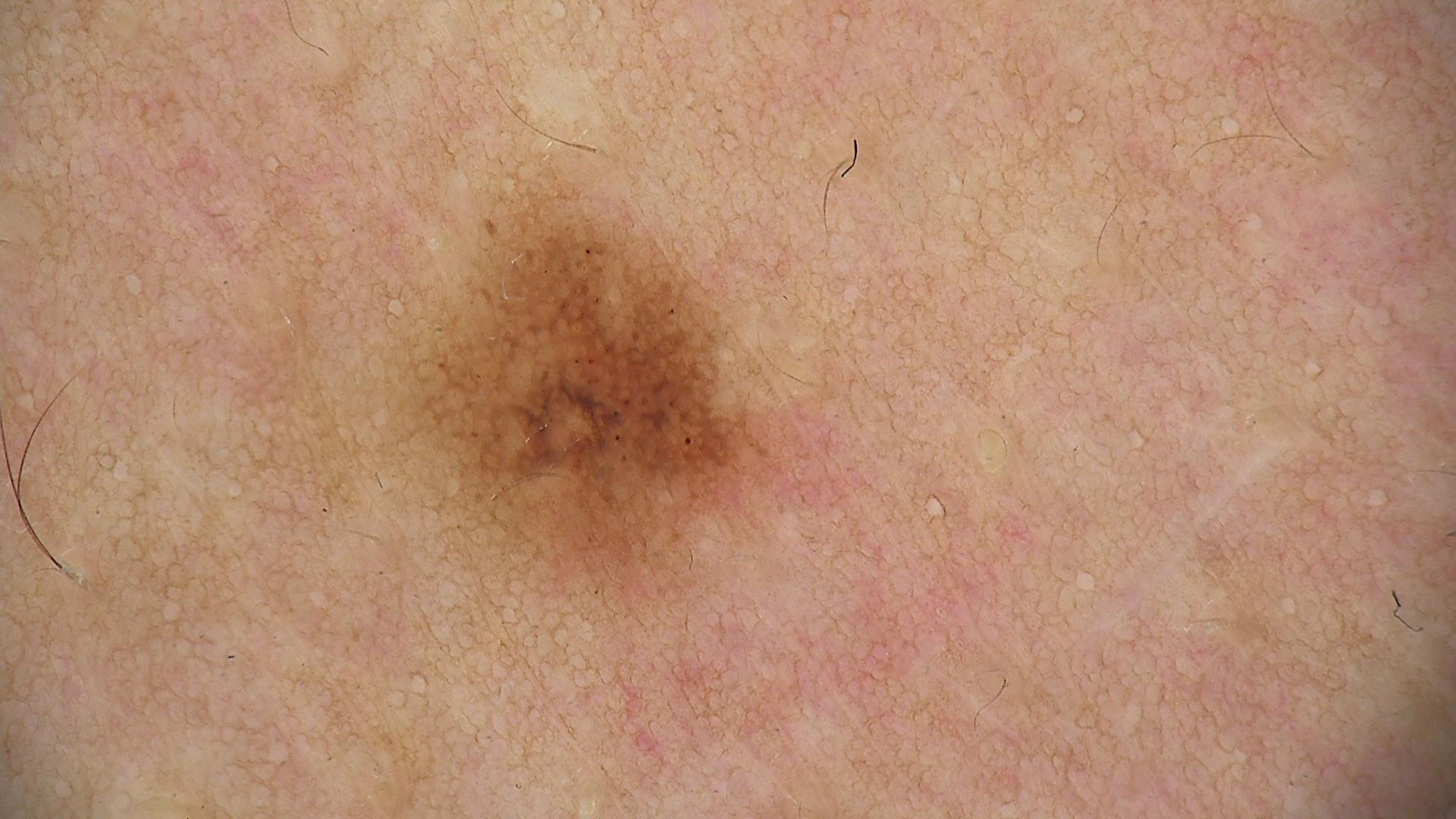<lesion>
  <image>dermatoscopy</image>
  <diagnosis>
    <name>dysplastic junctional nevus</name>
    <code>jd</code>
    <malignancy>benign</malignancy>
    <super_class>melanocytic</super_class>
    <confirmation>expert consensus</confirmation>
  </diagnosis>
</lesion>